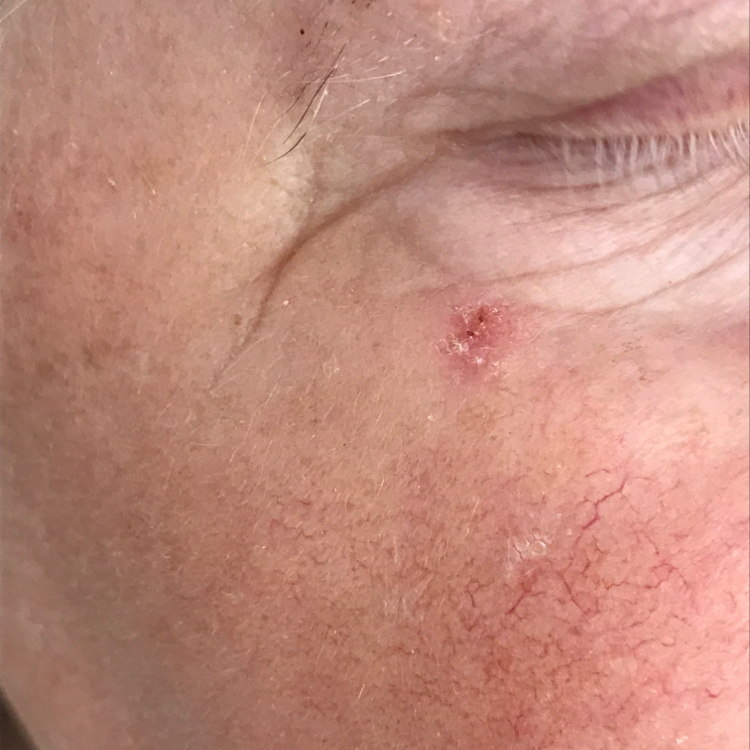{
  "diagnosis": {
    "name": "actinic keratosis",
    "code": "ACK",
    "malignancy": "indeterminate",
    "confirmation": "clinical consensus"
  }
}